A dermoscopic close-up of a skin lesion: 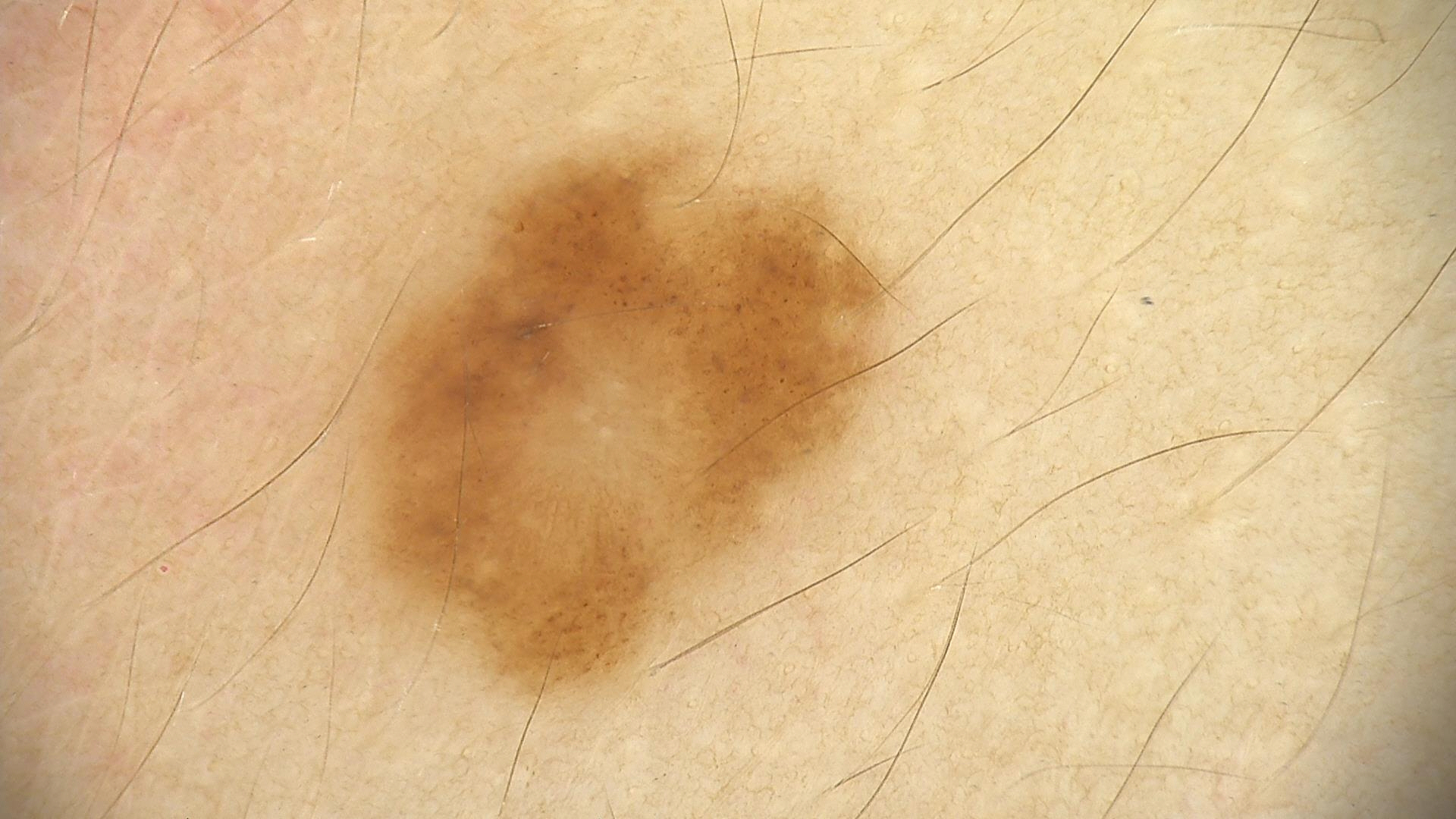Classified as a dysplastic junctional nevus.